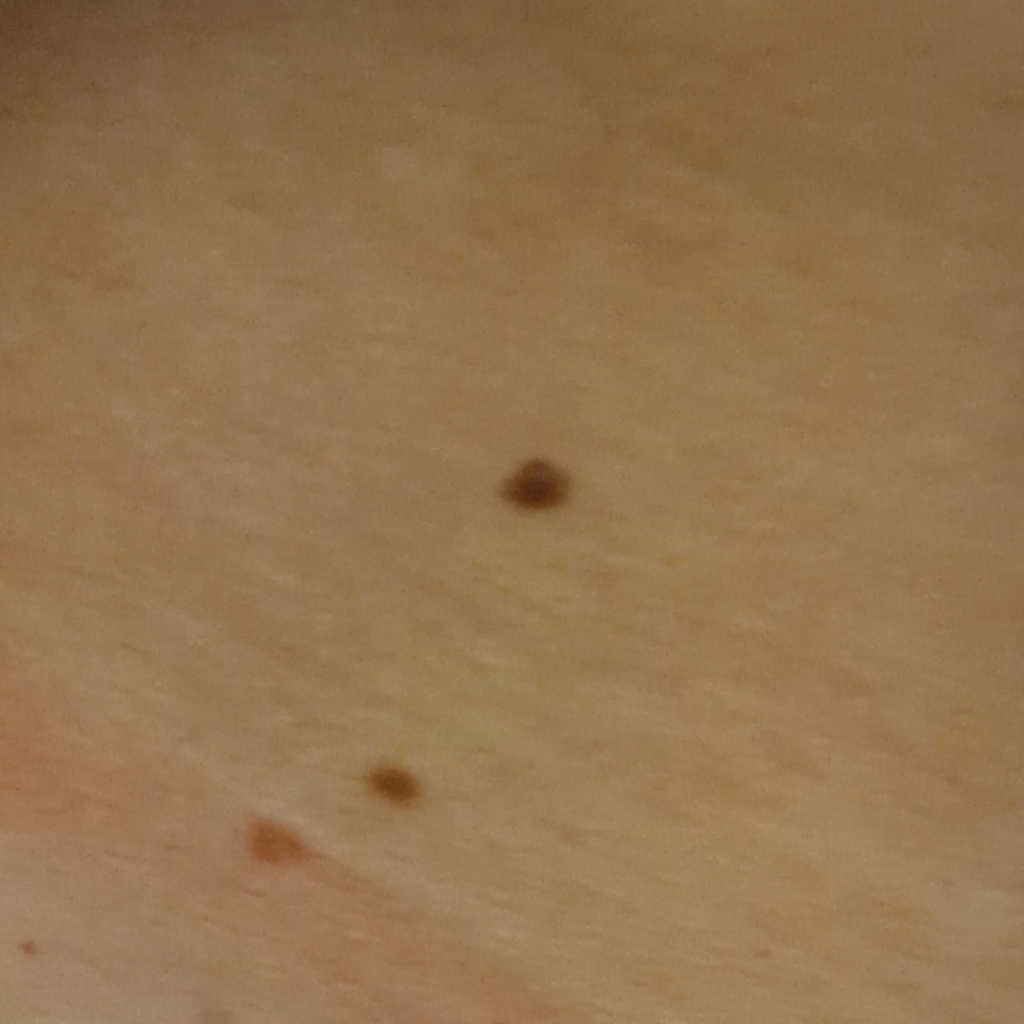A female subject age 48.
The patient reports a history of sunbed use and a family history of skin cancer.
Collected as part of a research study, without a referral diagnosis.
The patient says their skin reddens painfully with sun exposure.
Few moles overall by the patient's own estimate.
The lesion involves the torso.
The lesion measures approximately 4.3 mm.
Dermatologist review favored a melanocytic nevus.